Female subject, age 18–29; located on the head or neck and front of the torso; a close-up photograph: 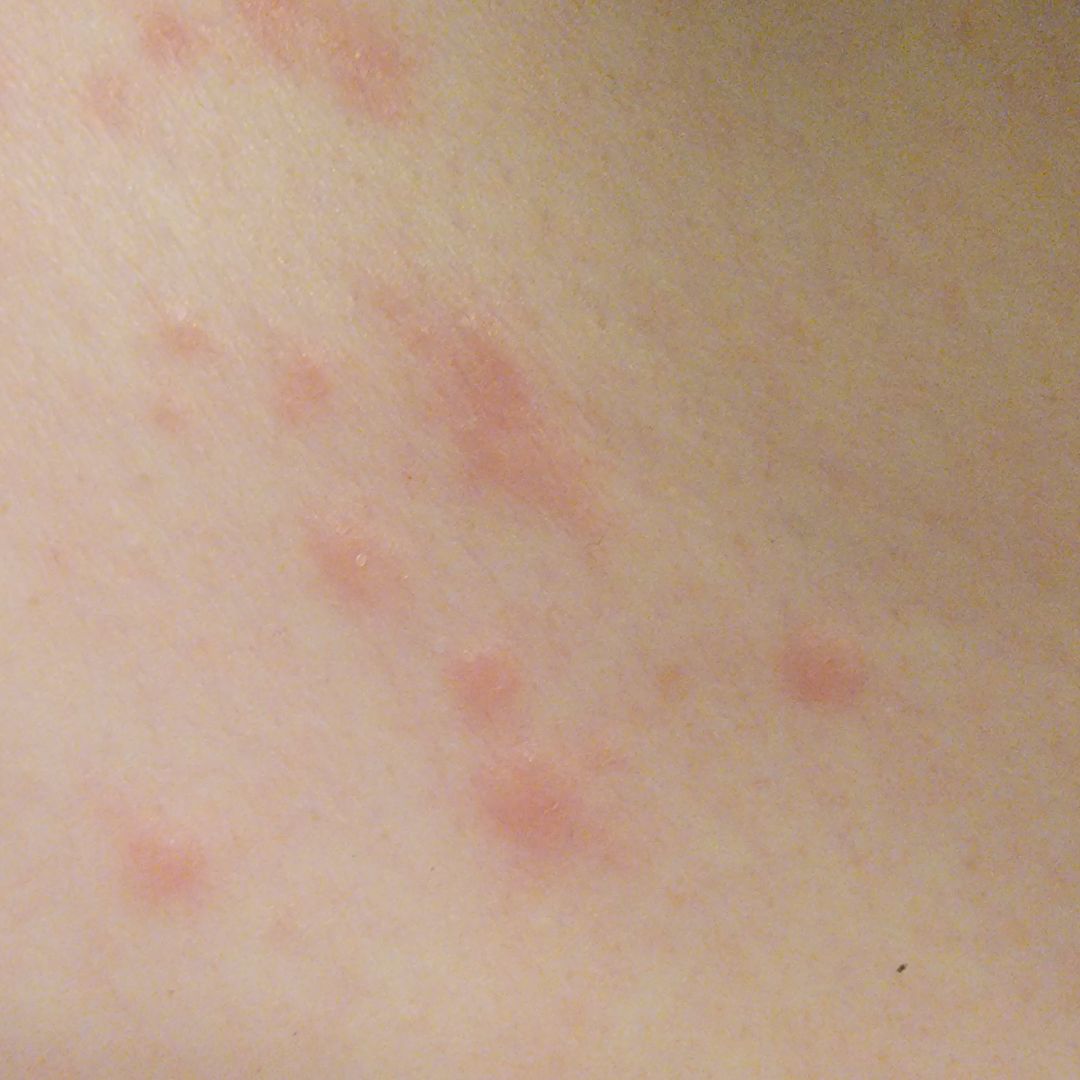<case>
<assessment>unable to determine</assessment>
<skin_tone>
  <fitzpatrick>II</fitzpatrick>
</skin_tone>
<symptoms>bothersome appearance, enlargement</symptoms>
</case>